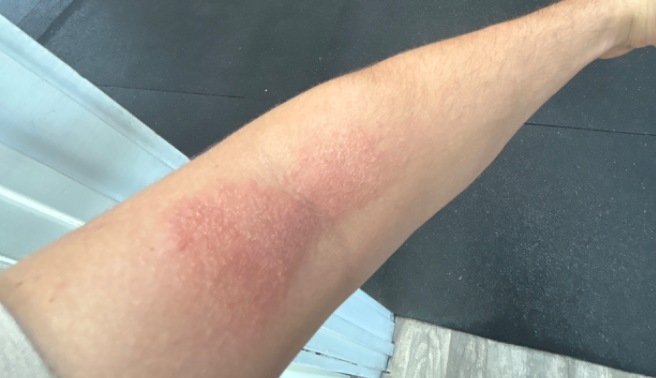Patient information: The contributor is 18–29, male. The arm is involved. The photograph was taken at a distance. Texture is reported as rough or flaky. The patient indicates itching and burning. Self-categorized by the patient as a rash. The patient indicates the condition has been present for less than one week. Review: Favoring Lichen Simplex Chronicus; possibly Psoriasis.